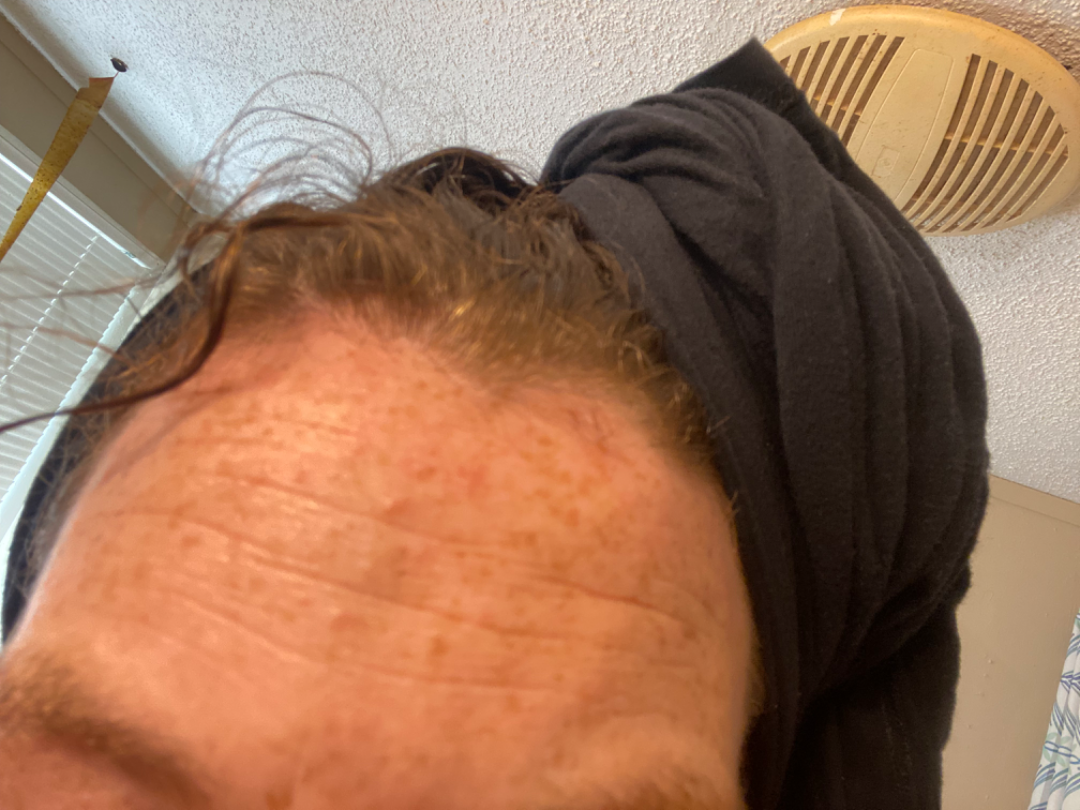Case summary:
• view — at an angle
• body site — head or neck
• patient describes the issue as — a rash
• symptoms — bothersome appearance, burning, pain and itching
• skin tone — Fitzpatrick phototype III; lay reviewers estimated MST 5 (US pool) or 2 (India pool)
• patient — female, age 30–39
• onset — less than one week
• described texture — flat, raised or bumpy and rough or flaky
• dermatologist impression — Acne (0.50); Folliculitis (0.33); Allergic Contact Dermatitis (0.17)